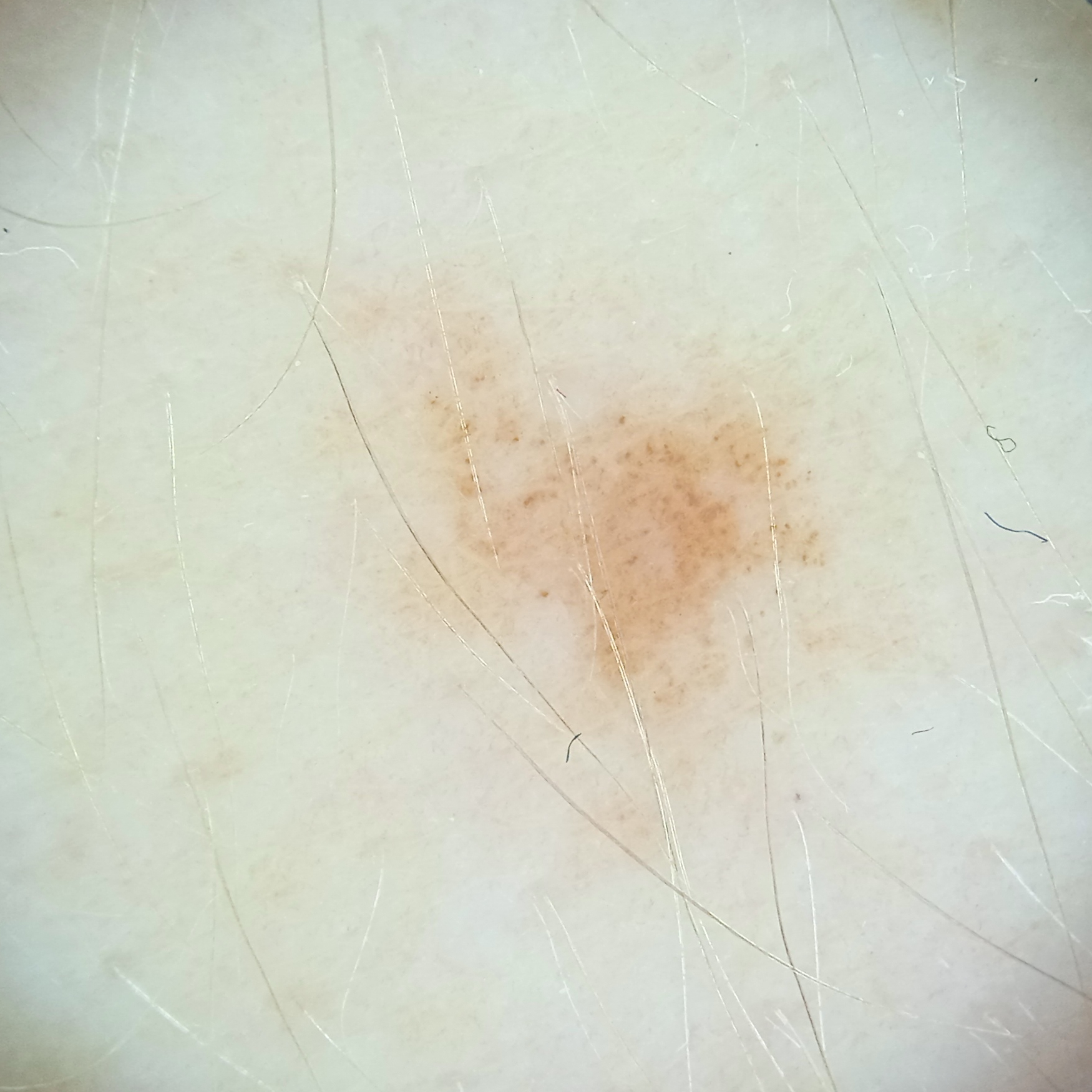Q: Why was this imaged?
A: research study (no referral diagnosis)
Q: What kind of image is this?
A: dermoscopic image
Q: How large is the lesion?
A: 5.1 mm
Q: What was the diagnosis?
A: melanocytic nevus (dermatologist consensus)